The lesion involves the front of the torso and arm. A close-up photograph. The patient considered this a rash. The contributor reports the condition has been present for one to four weeks. The contributor reports itching. The subject is 40–49, male. Skin tone: Fitzpatrick phototype II; human graders estimated 2 on the Monk skin tone scale. The contributor reports the lesion is raised or bumpy — 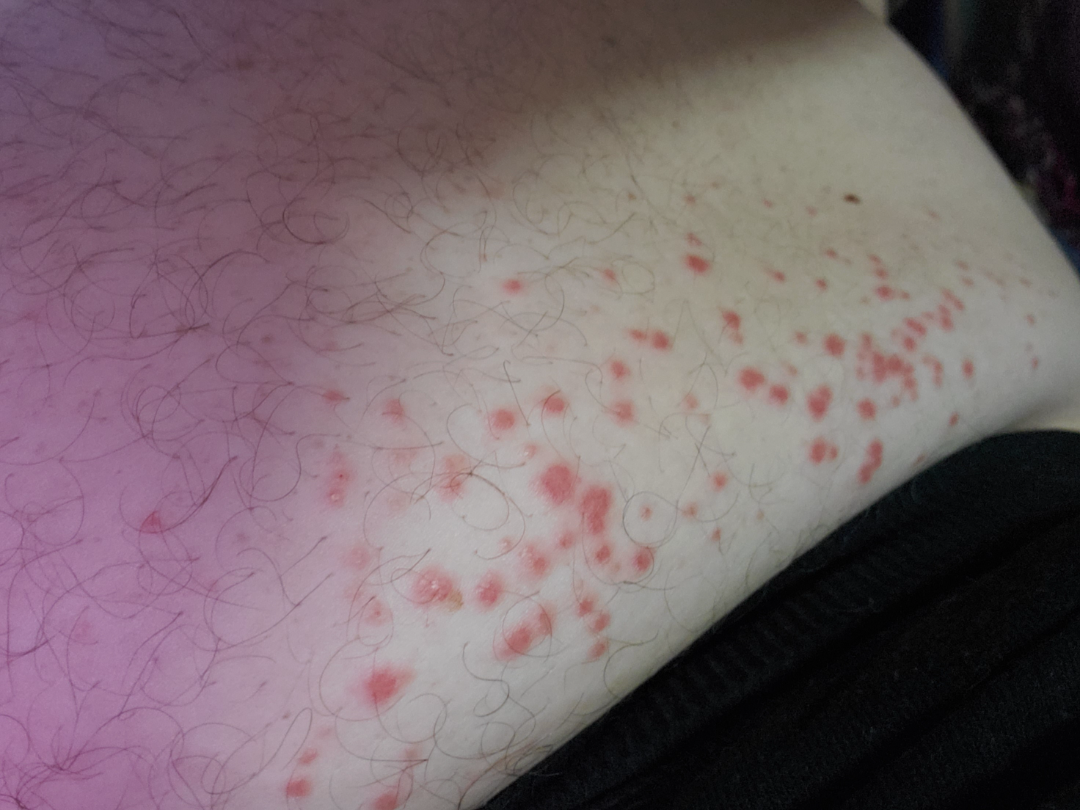dermatologist impression=most consistent with Leukocytoclastic Vasculitis.